Female patient, age 60–69. Located on the arm, leg and front of the torso. Reported duration is about one day. Skin tone: Fitzpatrick phototype II. Reported lesion symptoms include bothersome appearance and burning. Self-categorized by the patient as a rash. Close-up view. Texture is reported as raised or bumpy: 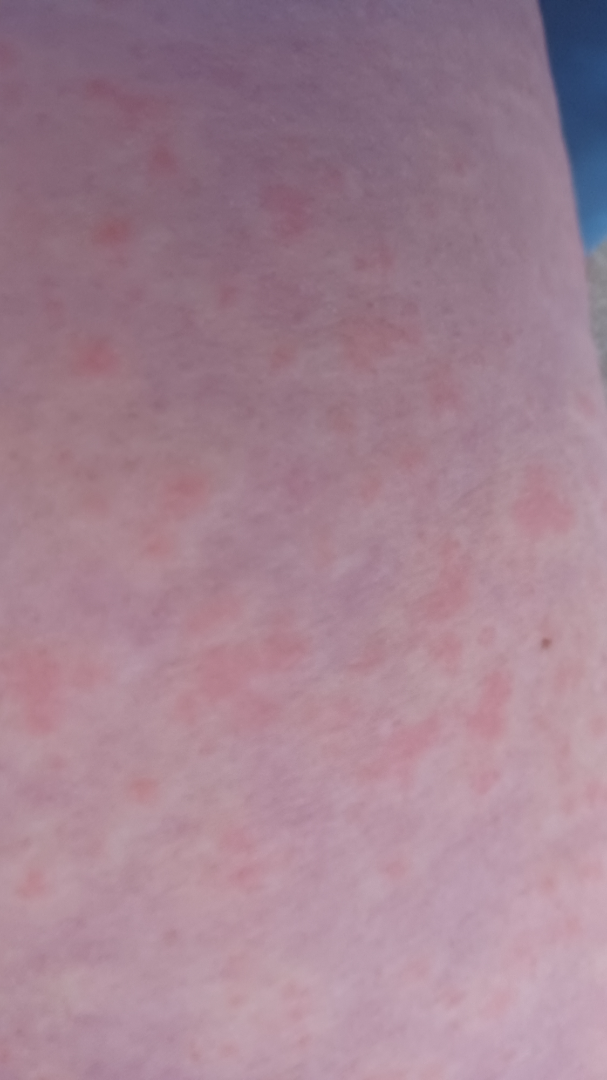The reviewing dermatologist was unable to assign a differential diagnosis from the image.